The lesion involves the arm and front of the torso. The patient indicates bothersome appearance and burning. The patient indicates the condition has been present for less than one week. This image was taken at an angle. The subject is male. The patient indicates the lesion is fluid-filled. Self-categorized by the patient as a rash:
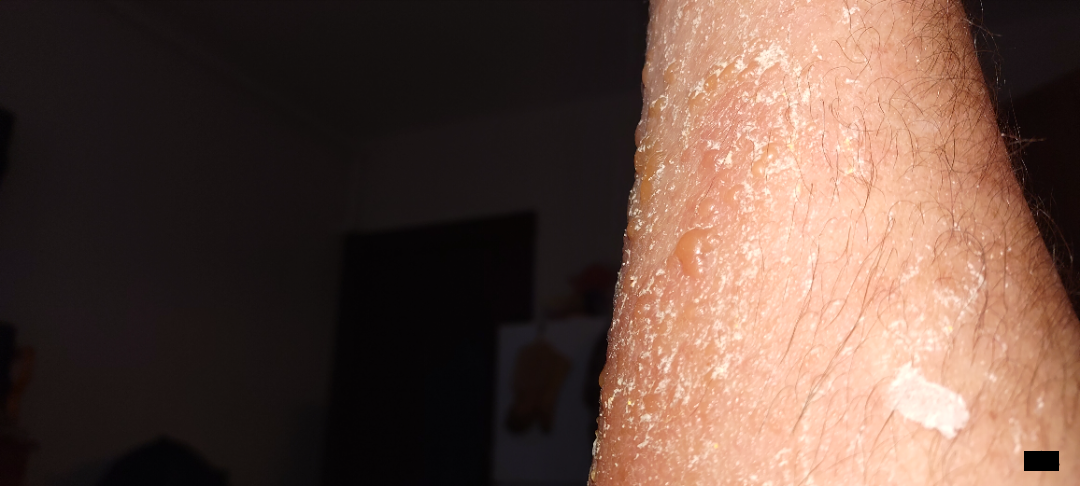Case summary:
• dermatologist impression — the favored diagnosis is Bullous Pemphigoid